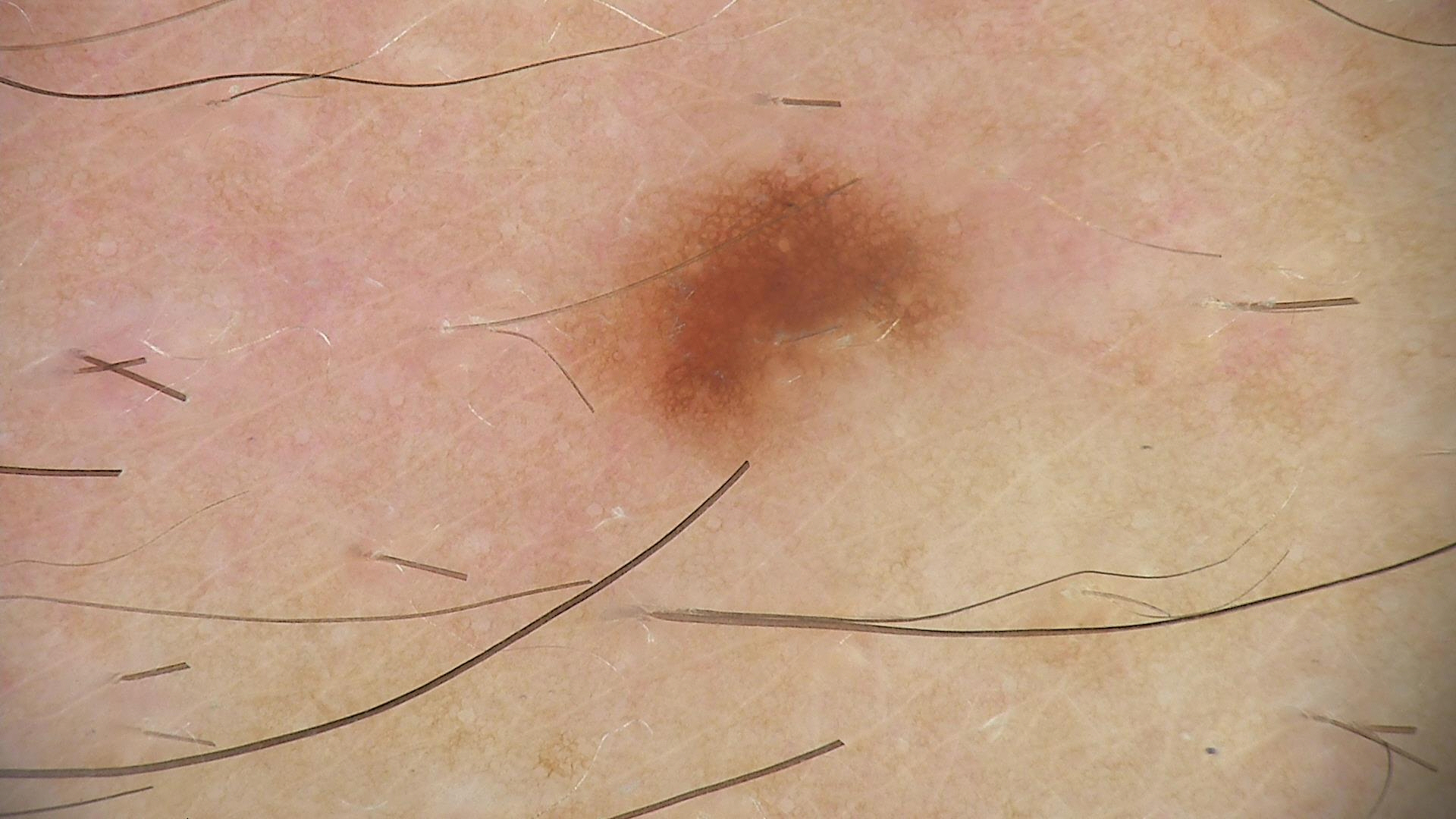Classified as a dysplastic junctional nevus.